The photograph was taken at a distance: 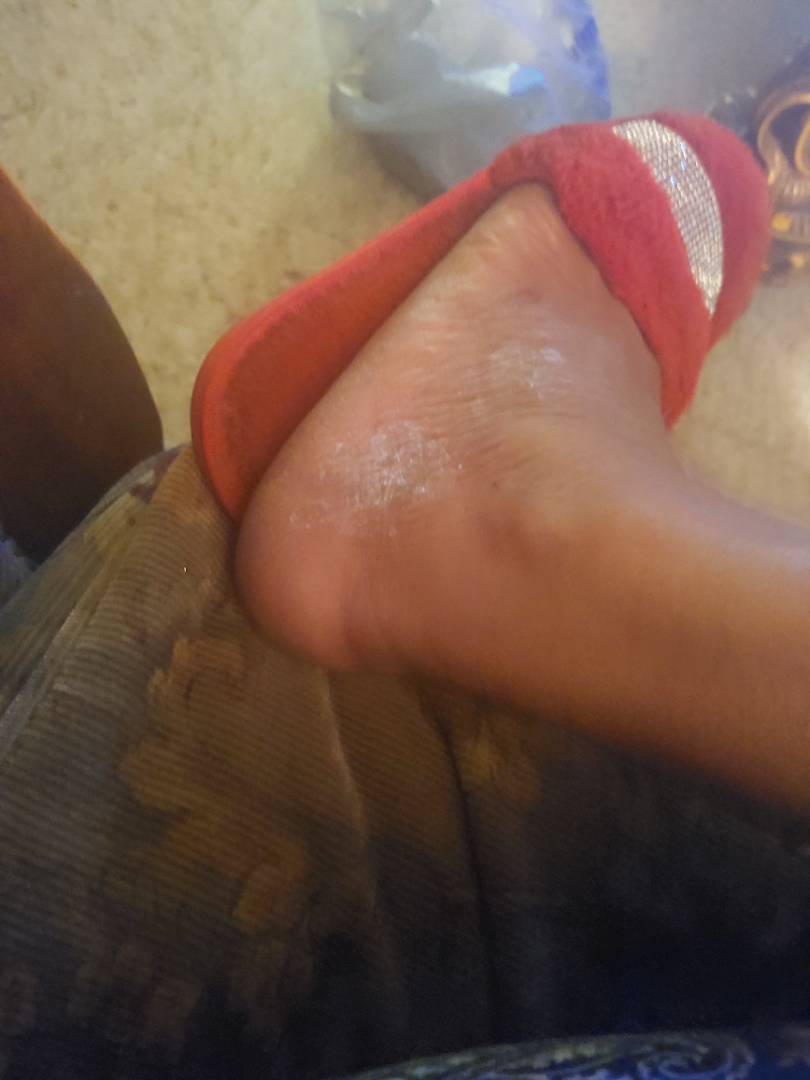The differential includes Psoriasis and Eczema, with no clear leading consideration; less likely is Tinea.